Skin tone: FST III; lay reviewers estimated MST 2 or 3 (two reviewer pools). Reported lesion symptoms include bothersome appearance, burning, darkening, enlargement and pain. The contributor notes the condition has been present for one to four weeks. The contributor notes the lesion is raised or bumpy. Self-categorized by the patient as a rash. The leg is involved. An image taken at a distance:
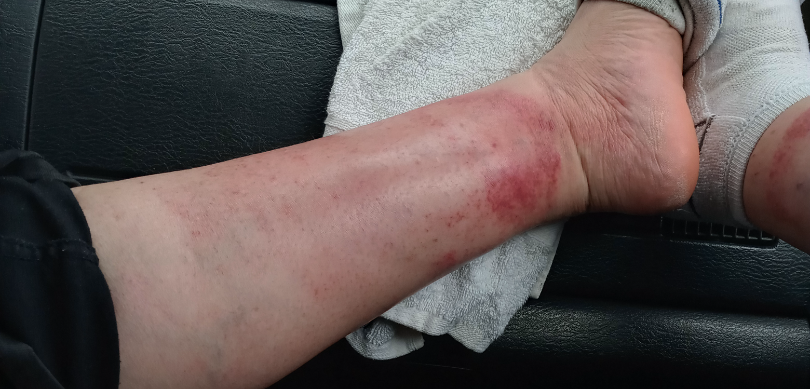Notes:
• differential diagnosis — favoring Stasis Dermatitis; also consider Pigmented purpuric eruption; a remote consideration is Eczema